The arm is involved. The patient considered this a rash. Male subject, age 18–29. A close-up photograph. Fitzpatrick phototype II; human graders estimated MST 1 (US pool) or 2 (India pool) — 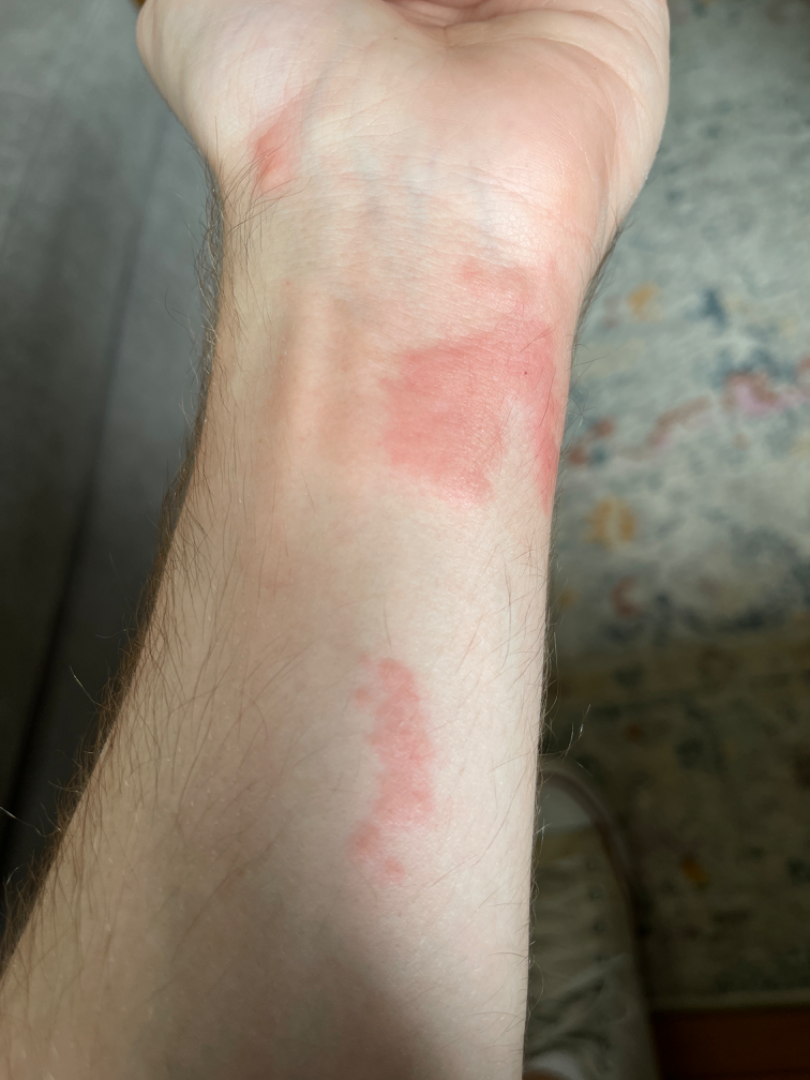  differential:
    leading:
      - Allergic Contact Dermatitis
    considered:
      - Urticaria
      - Insect Bite